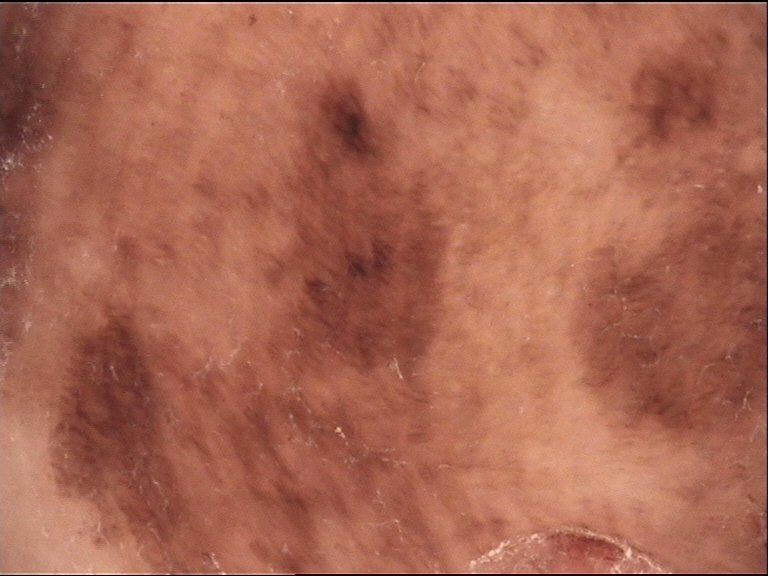<dermoscopy>
  <image>dermoscopy</image>
  <diagnosis>
    <name>acral lentiginous melanoma</name>
    <code>alm</code>
    <malignancy>malignant</malignancy>
    <super_class>melanocytic</super_class>
    <confirmation>histopathology</confirmation>
  </diagnosis>
</dermoscopy>